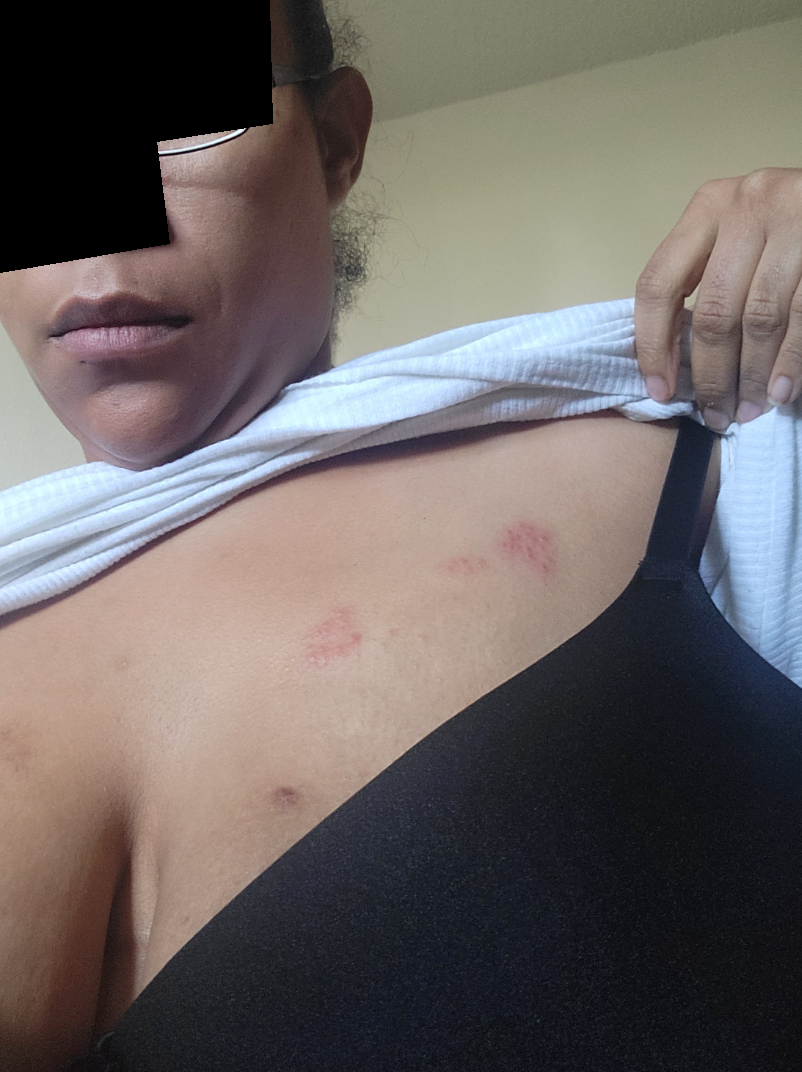history: less than one week | view: at a distance | patient-reported symptoms: itching, pain and burning | patient describes the issue as: a rash | skin tone: Fitzpatrick IV; lay graders estimated MST 4 or 5 (two reviewer pools) | lesion texture: raised or bumpy | dermatologist impression: Herpes Zoster (most likely); Contact dermatitis (lower probability); Allergic Contact Dermatitis (lower probability); Herpes Simplex (lower probability).